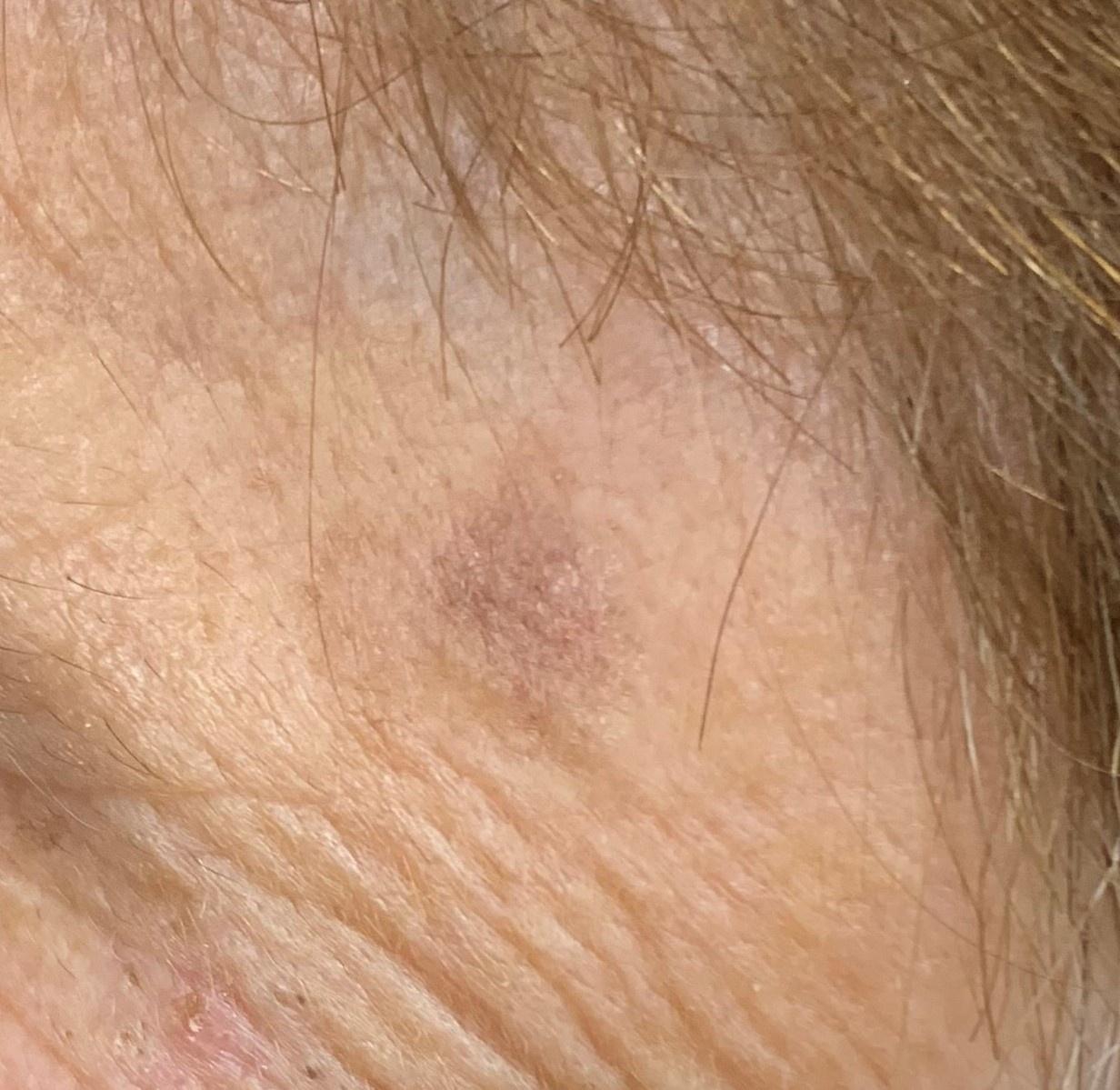subject: female, in their 70s
FST: II
image: clinical photo (overview)
anatomic site: the head or neck
impression: Solar or actinic keratosis